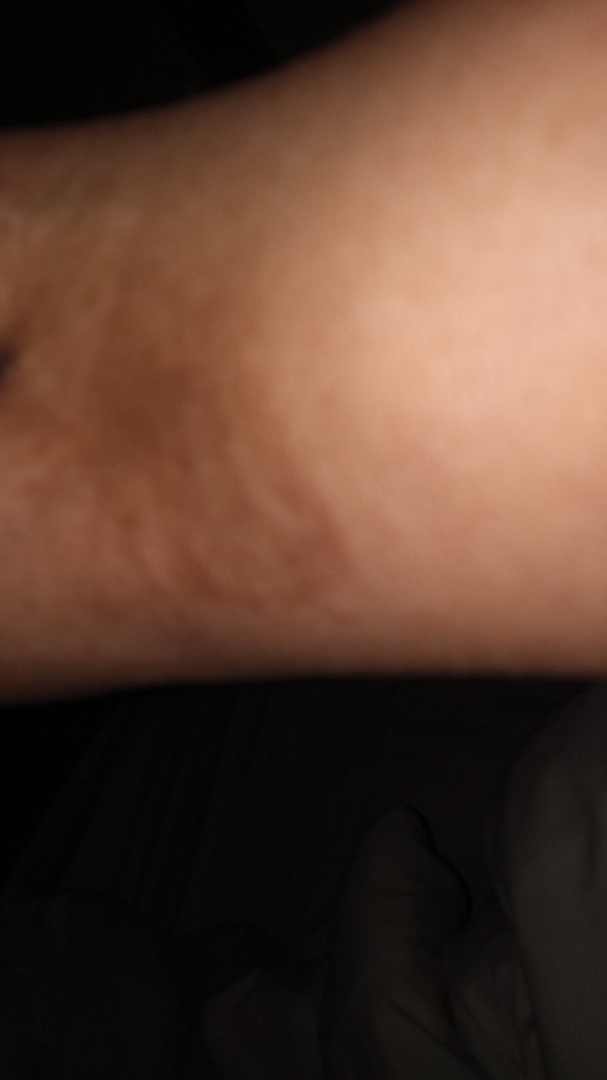Findings:
* image framing — close-up
* surface texture — raised or bumpy
* skin tone — self-reported Fitzpatrick skin type V
* subject — female, age 50–59